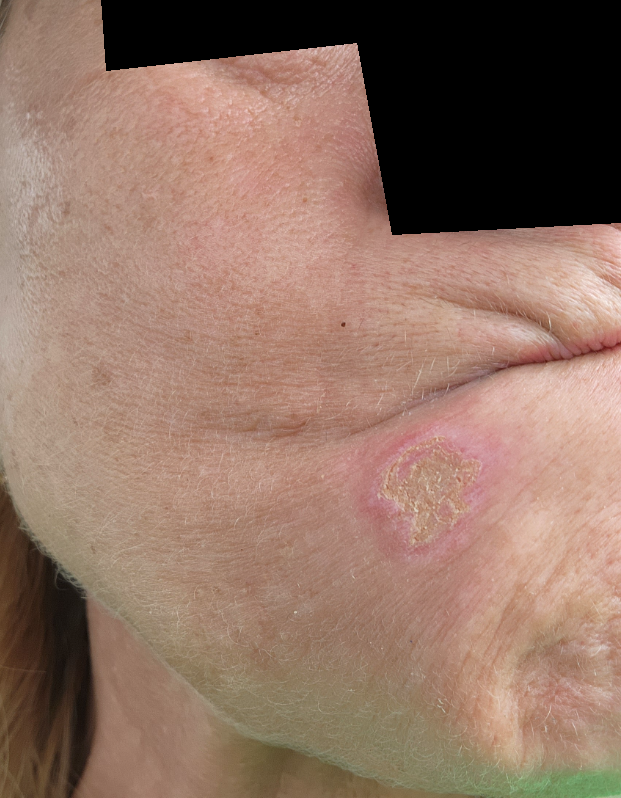Review: On teledermatology review: Eruptive odontogenic cyst, Basal Cell Carcinoma and SCC/SCCIS were considered with similar weight.